An image taken at an angle: 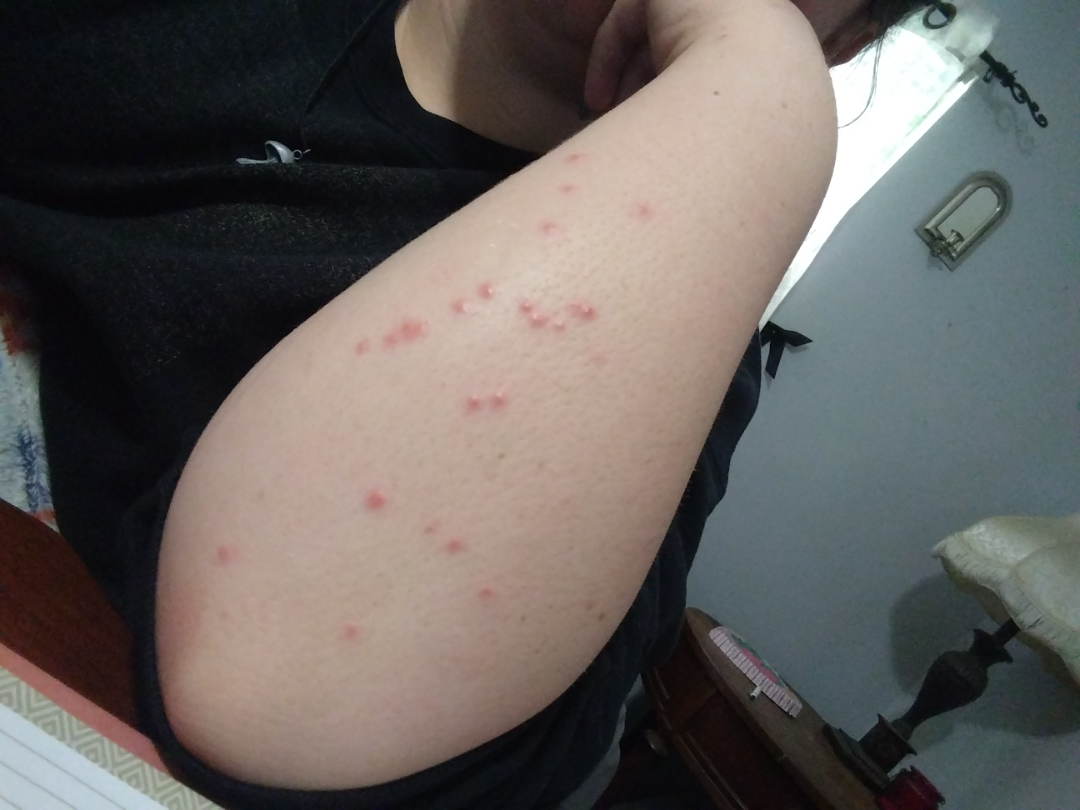differential diagnosis = the leading impression is Insect Bite; possibly Eczema; an alternative is Molluscum Contagiosum